Dermoscopy of a skin lesion:
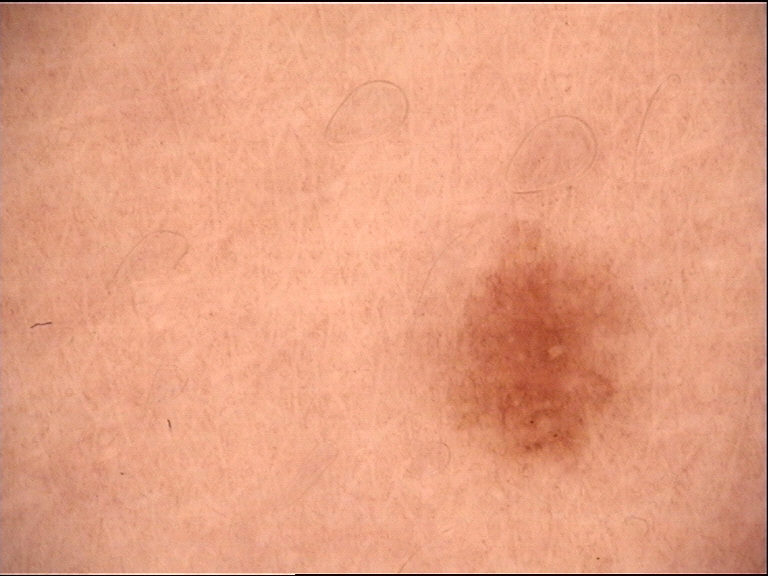diagnostic label: dysplastic junctional nevus (expert consensus)